Male patient, age 30–39 · an image taken at a distance · located on the leg.
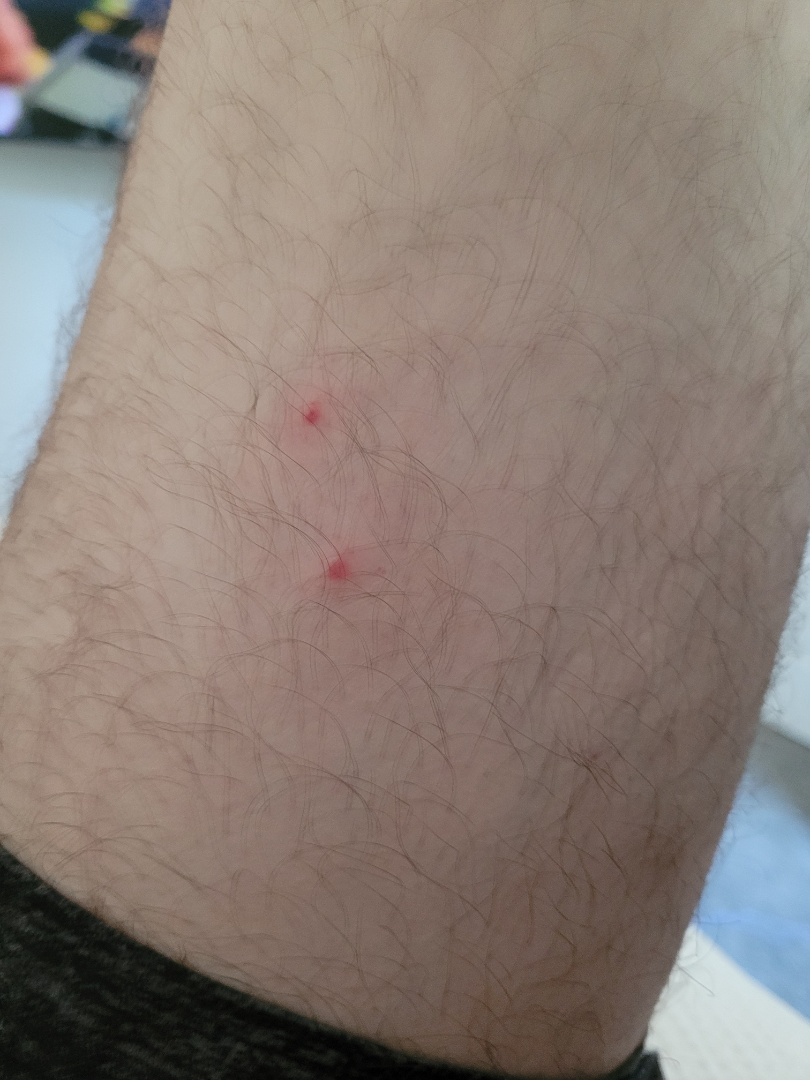Review:
The skin condition could not be confidently assessed from this image.